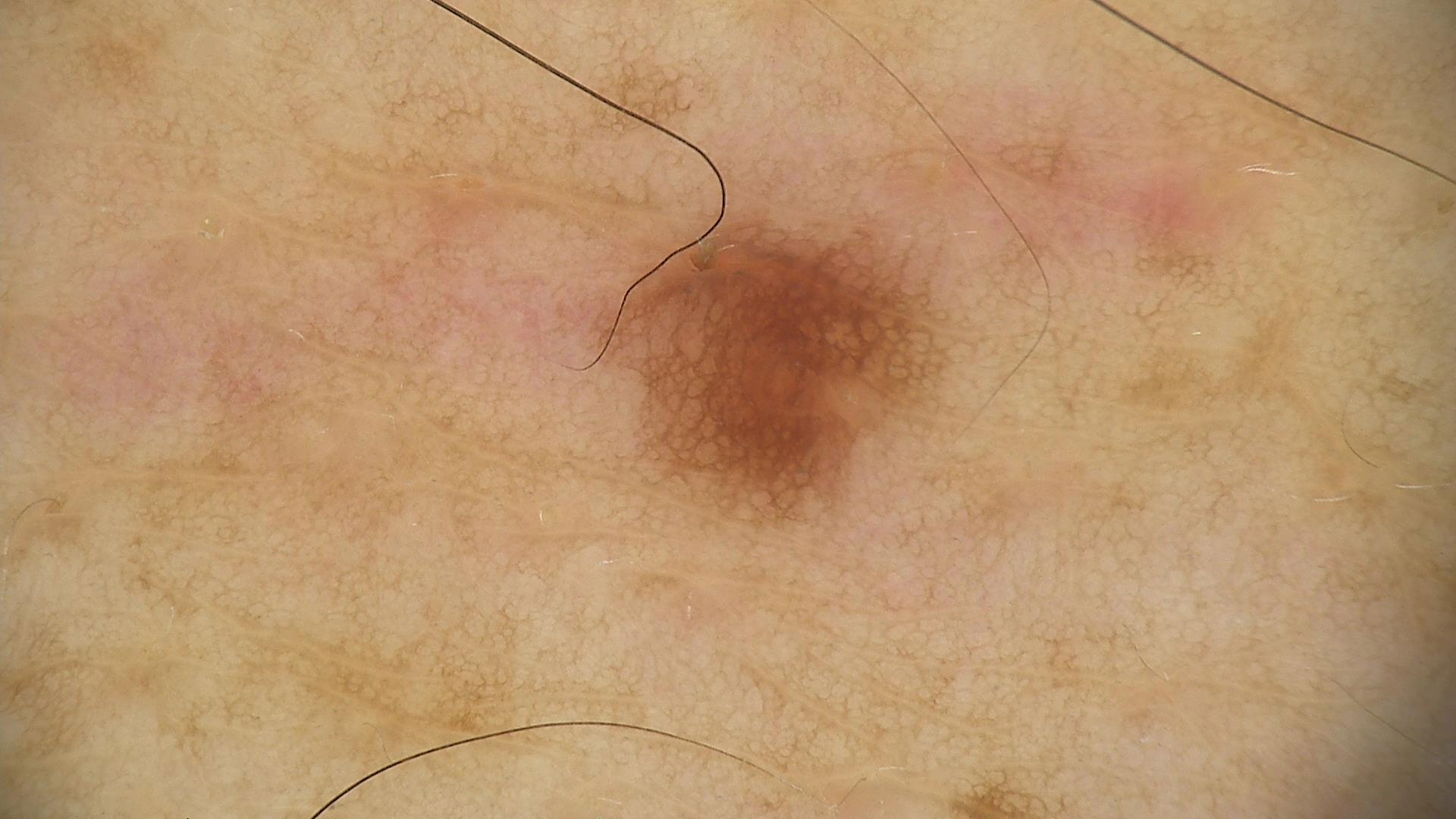Summary:
A dermoscopy image of a single skin lesion.
Impression:
The diagnostic label was a dysplastic junctional nevus.